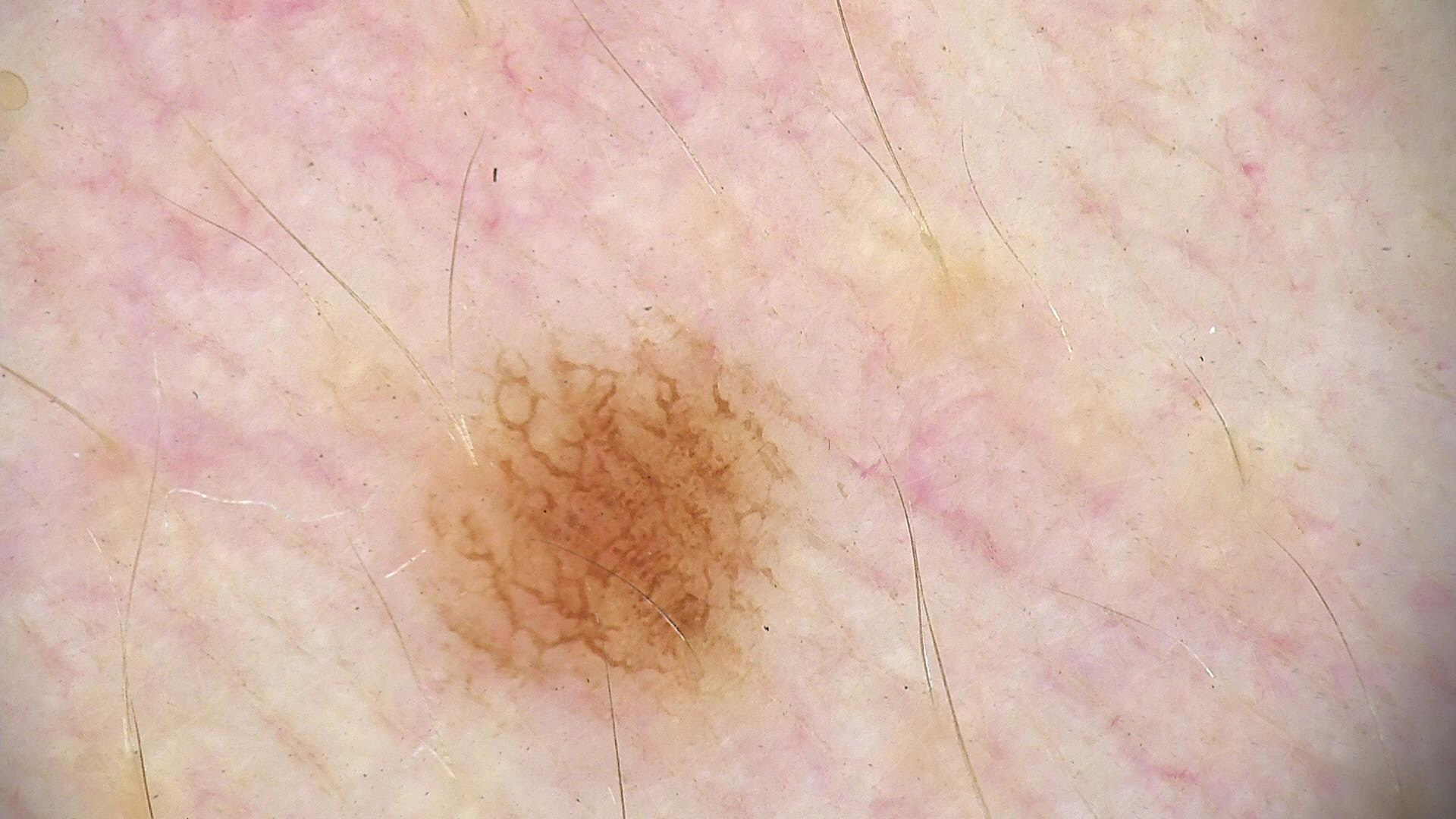<lesion>
<diagnosis>
<name>dysplastic junctional nevus</name>
<code>jd</code>
<malignancy>benign</malignancy>
<super_class>melanocytic</super_class>
<confirmation>expert consensus</confirmation>
</diagnosis>
</lesion>